This is a close-up image · the patient did not report lesion symptoms · no associated systemic symptoms reported · present for more than one year · the lesion is described as rough or flaky · skin tone: lay graders estimated Monk Skin Tone 1 or 2 (two reviewer pools) · the top or side of the foot is involved.
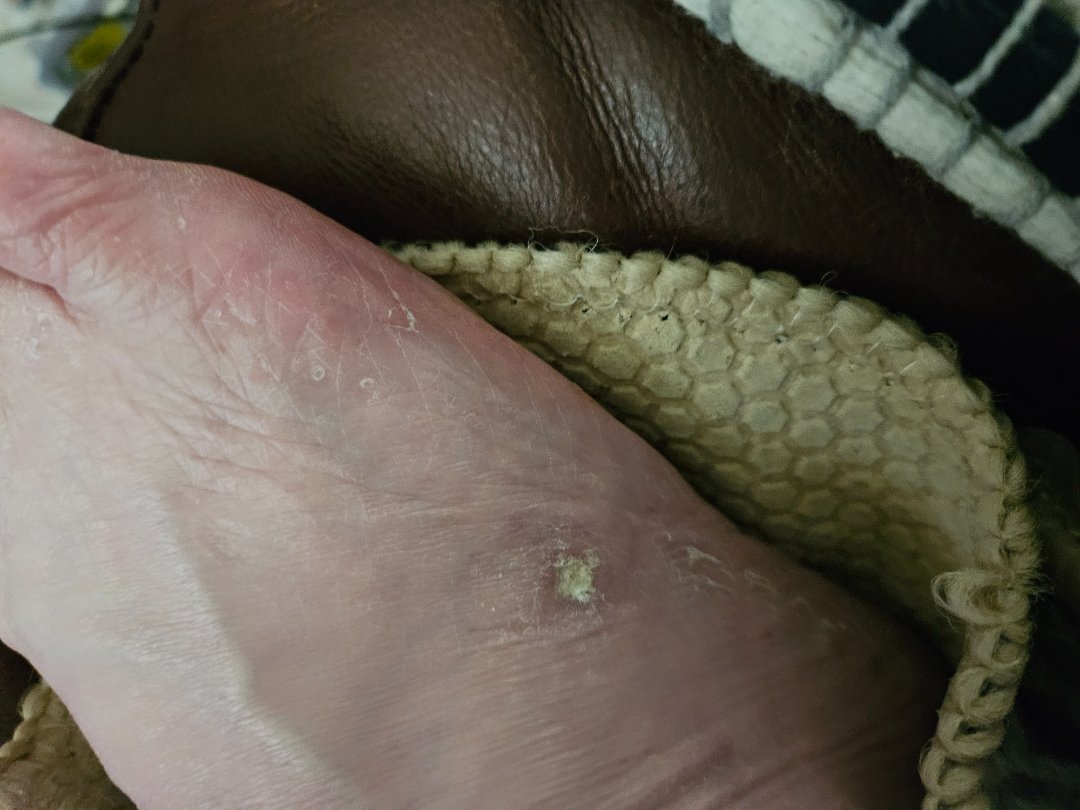Q: Could the case be diagnosed?
A: unable to determine